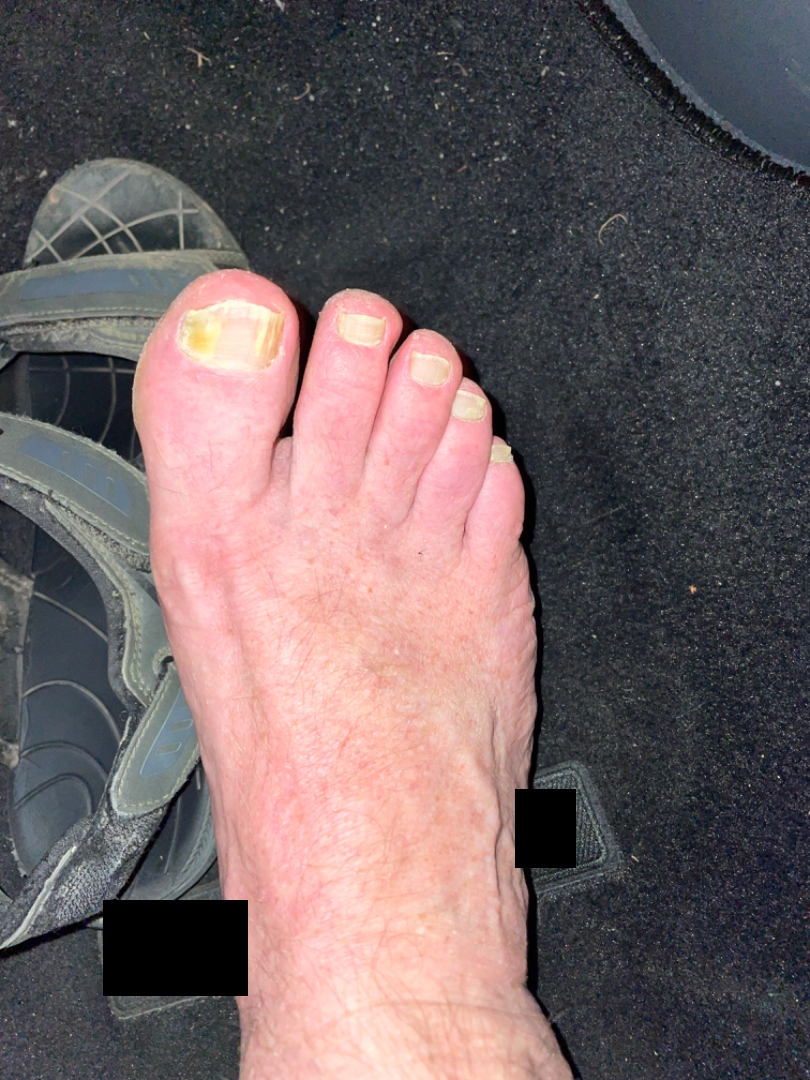Findings:
* clinical impression: most likely Onychomycosis; the differential also includes Psoriasis; also consider Nail dystrophy due to trauma